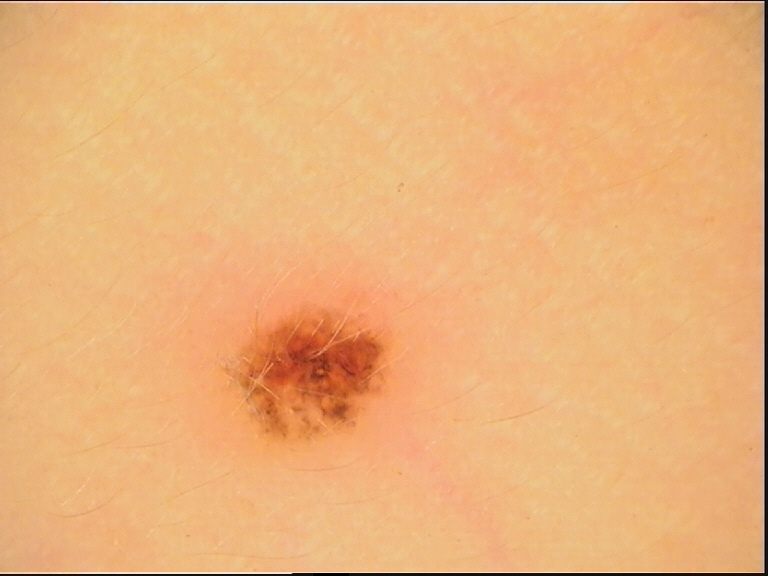diagnostic label: dysplastic junctional nevus (expert consensus).